The lesion involves the front of the torso, palm, head or neck, arm, back of the hand and leg. This is a close-up image:
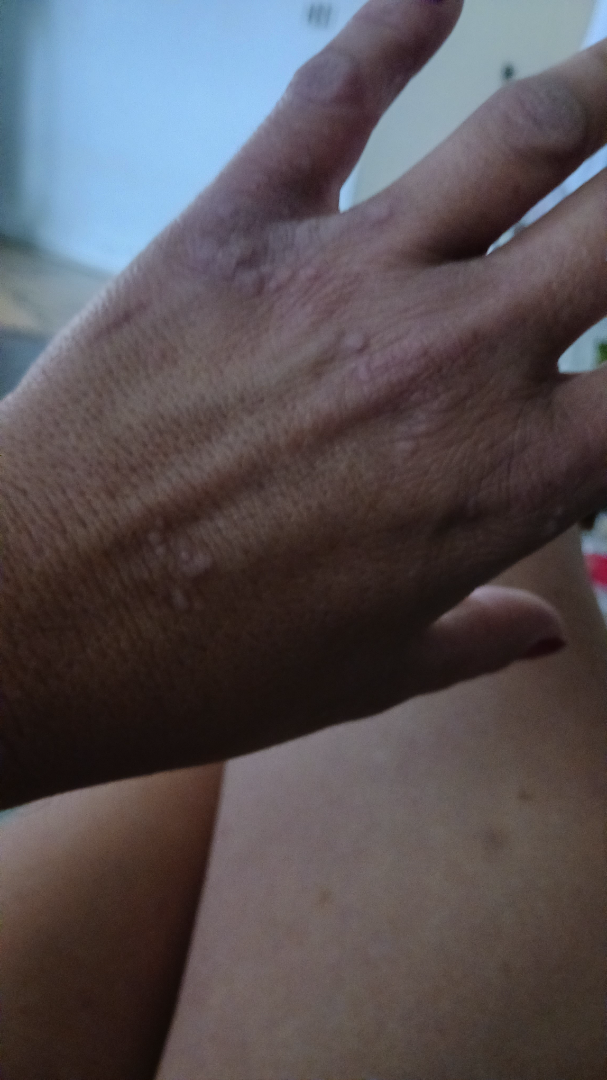Findings:
The reviewing clinician's impression was: Verruca vulgaris (67%); Lichen planus/lichenoid eruption (33%).